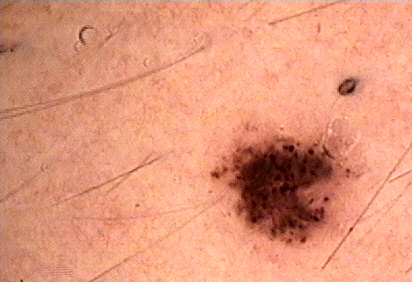Impression: The diagnostic label was a dysplastic compound nevus.